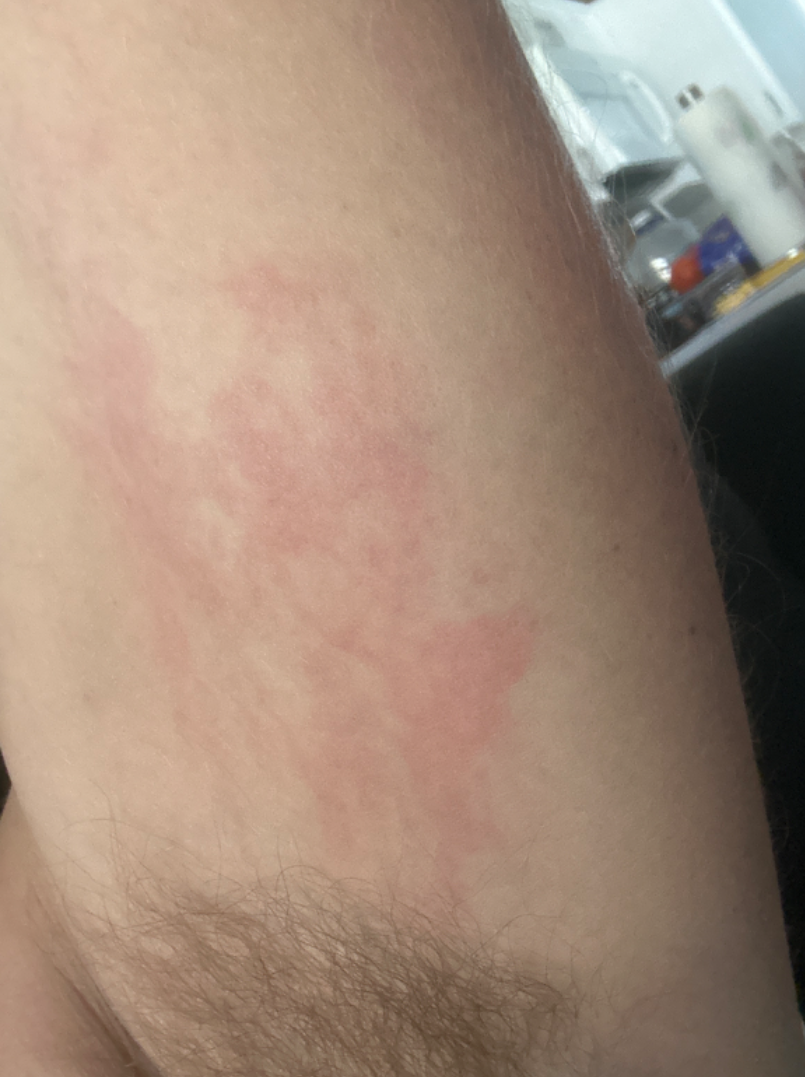The condition could not be reliably identified from the image.
The lesion involves the head or neck and arm.
The photograph is a close-up of the affected area.